A dermatoscopic image of a skin lesion. Few moles overall by the patient's own estimate. Referred with a clinical suspicion of basal cell carcinoma. A female subject 60 years old. The patient says their skin tans without first burning. By self-report, a personal history of skin cancer, a personal history of cancer, no sunbed use, and no family history of skin cancer.
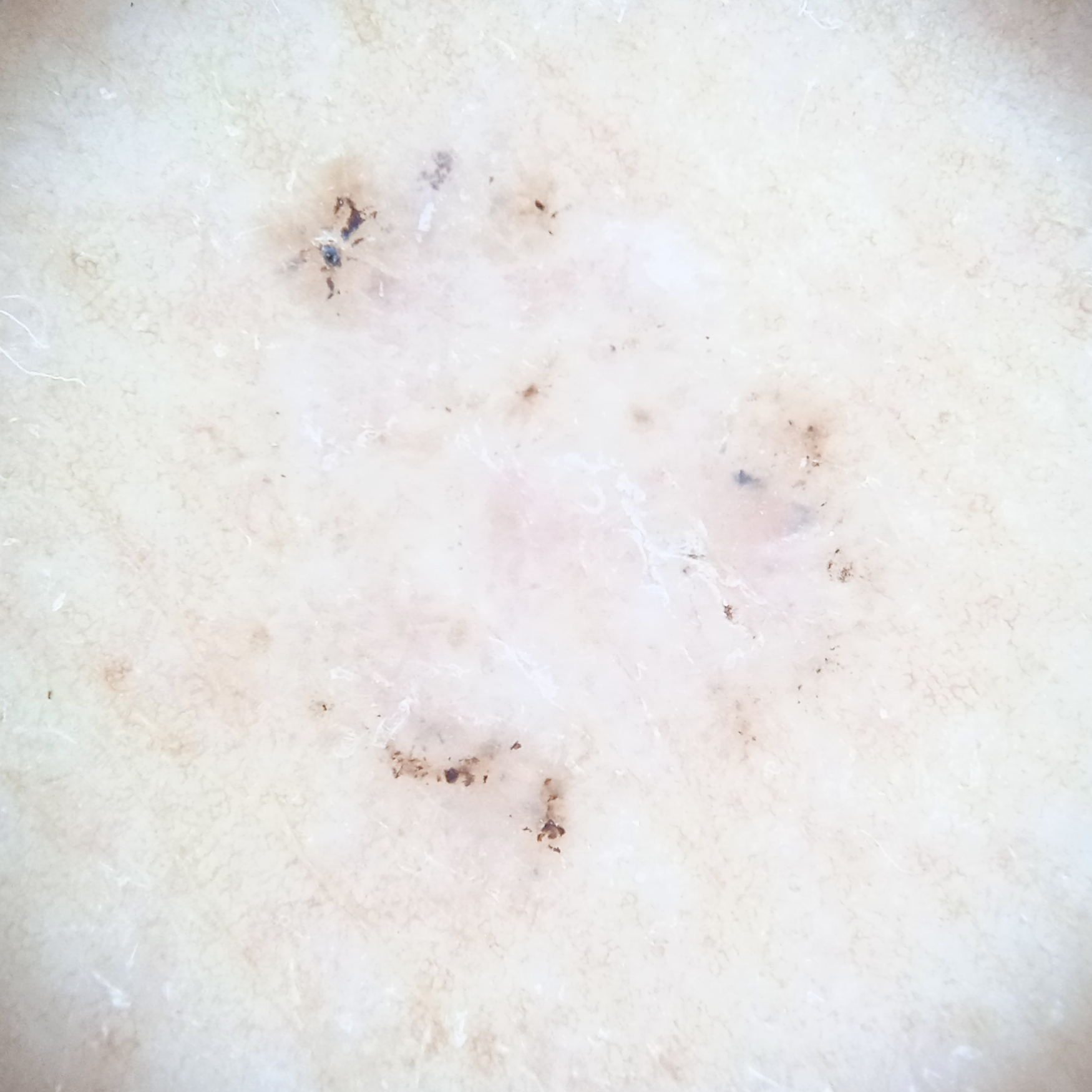Findings: The lesion is on the back. Measuring roughly 7.8 mm. Conclusion: The lesion was assessed as a basal cell carcinoma.